An image taken at a distance. The palm is involved. Female contributor, age 50–59:
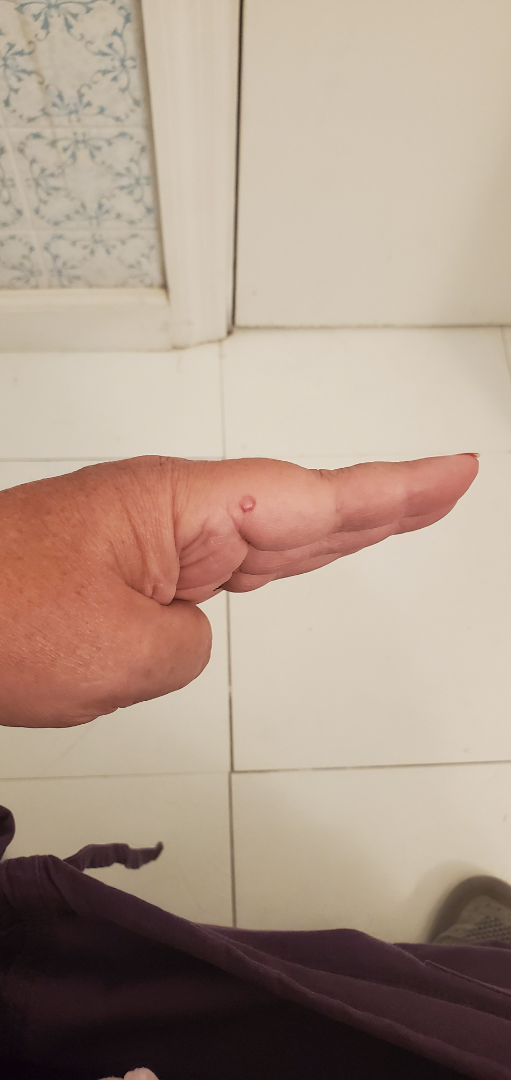The skin condition could not be confidently assessed from this image.
Self-categorized by the patient as skin that appeared healthy to them.
The lesion is described as rough or flaky and raised or bumpy.
No associated systemic symptoms reported.
Symptoms reported: darkening, pain and itching.